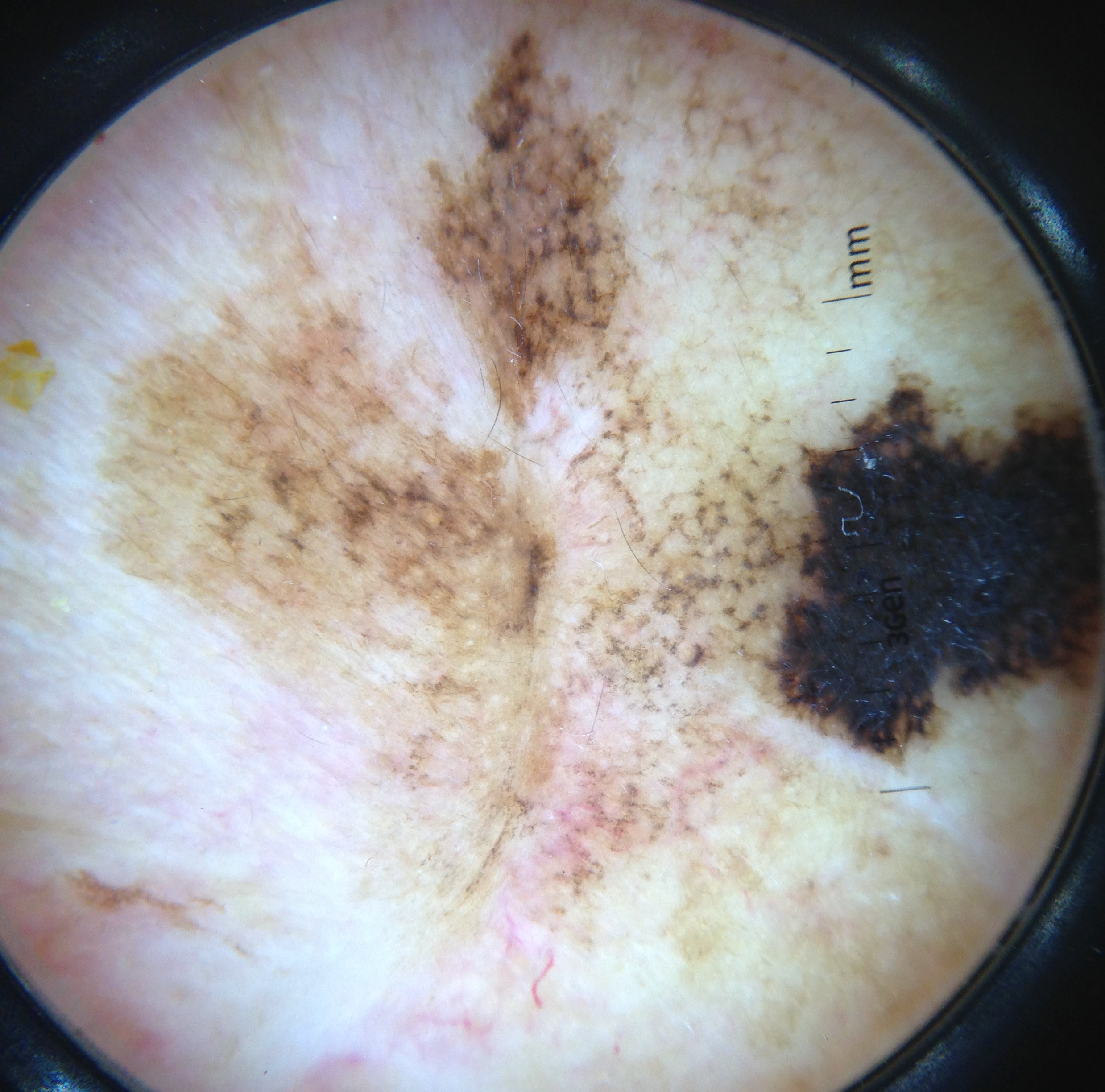Histopathology confirmed a lentigo maligna.